A female subject 55 years old. A clinical close-up of a skin lesion. The patient reports a prior organ transplant and immunosuppression. The patient describes having a moderate number of moles. Acquired for a research image collection, with no referral diagnosis. The patient says their skin reddens painfully with sun exposure: 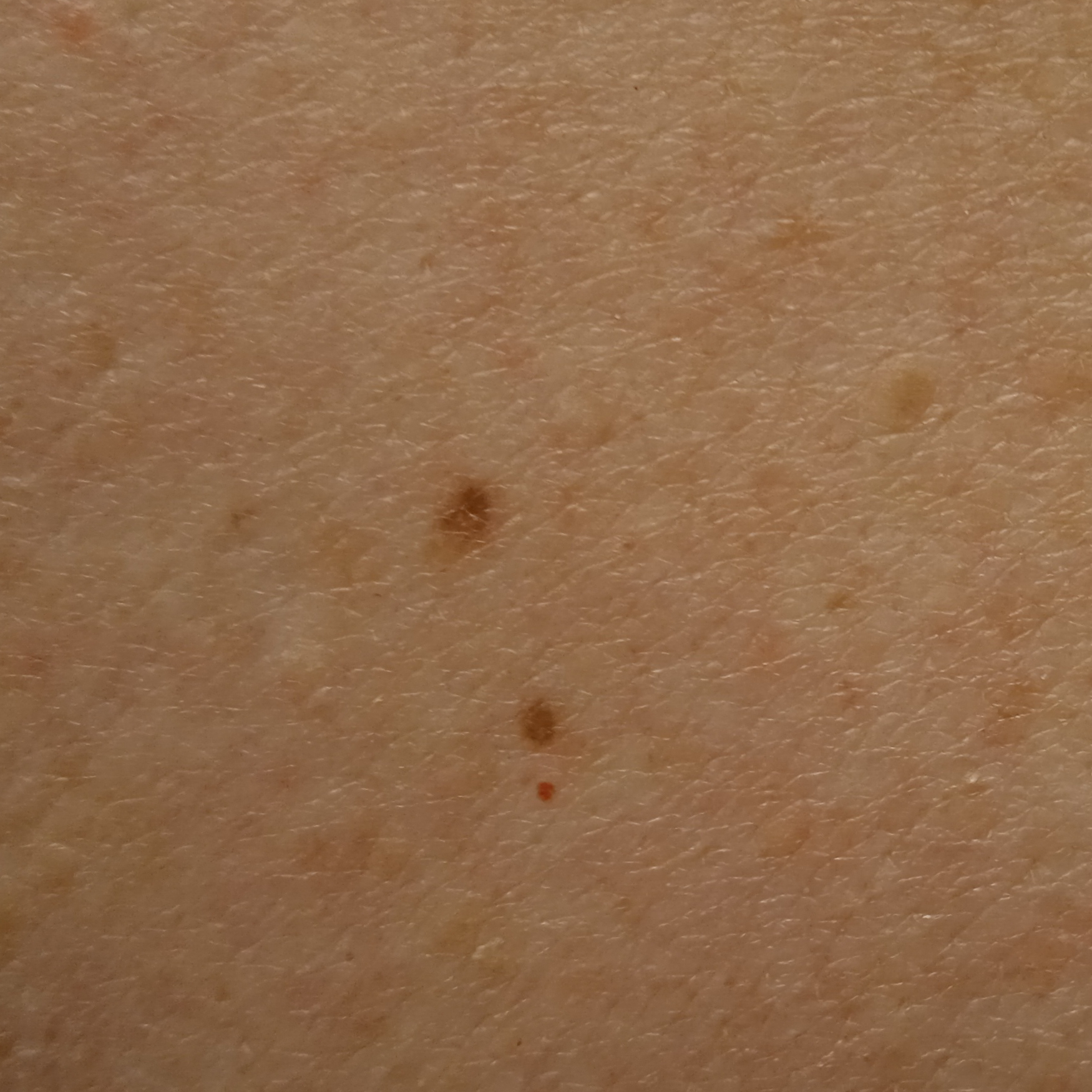Summary: Located on the back. Conclusion: The lesion was assessed as a melanocytic nevus.